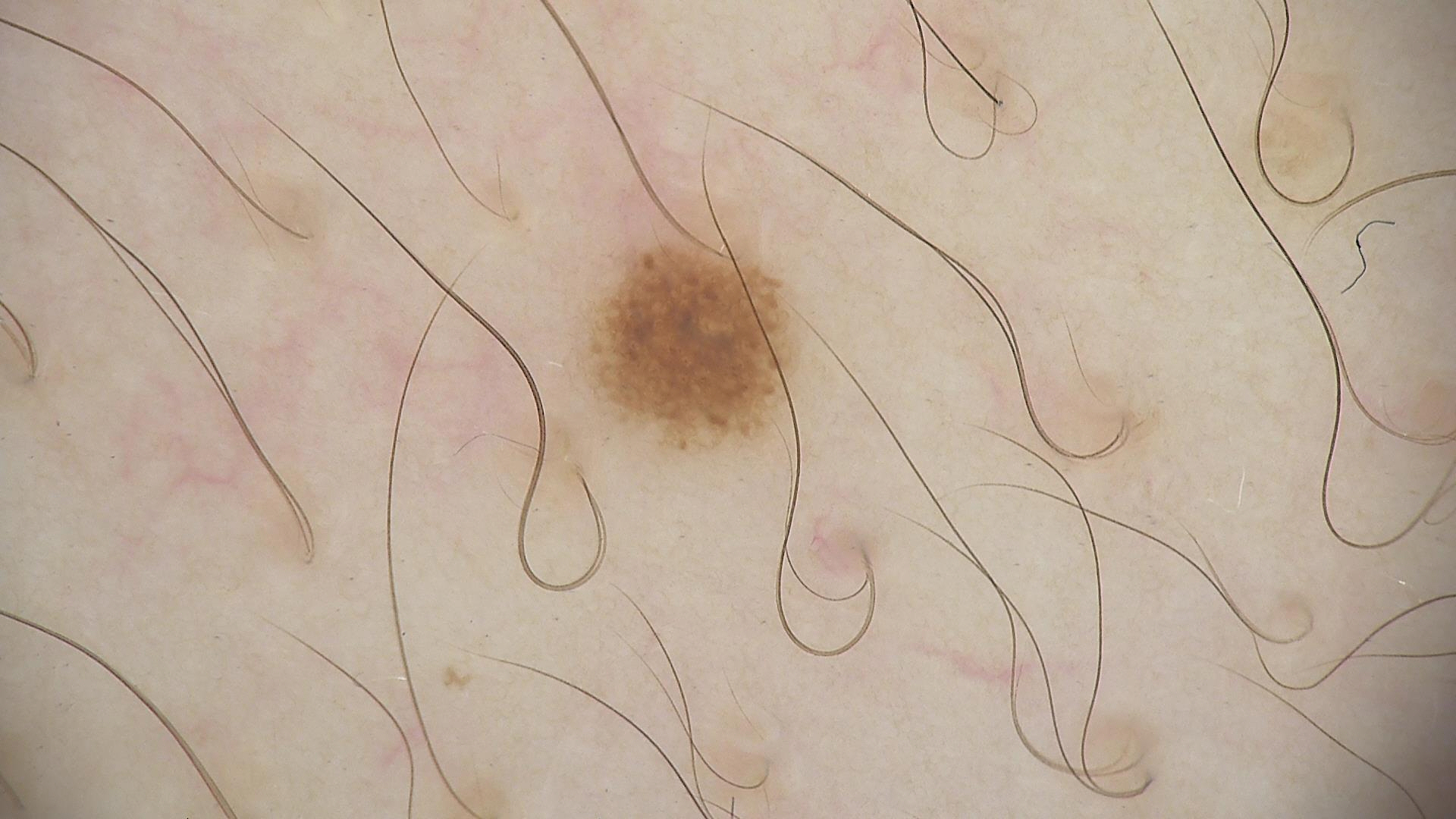| key | value |
|---|---|
| image | dermoscopy |
| class | dysplastic junctional nevus (expert consensus) |